A dermoscopic image of a skin lesion: 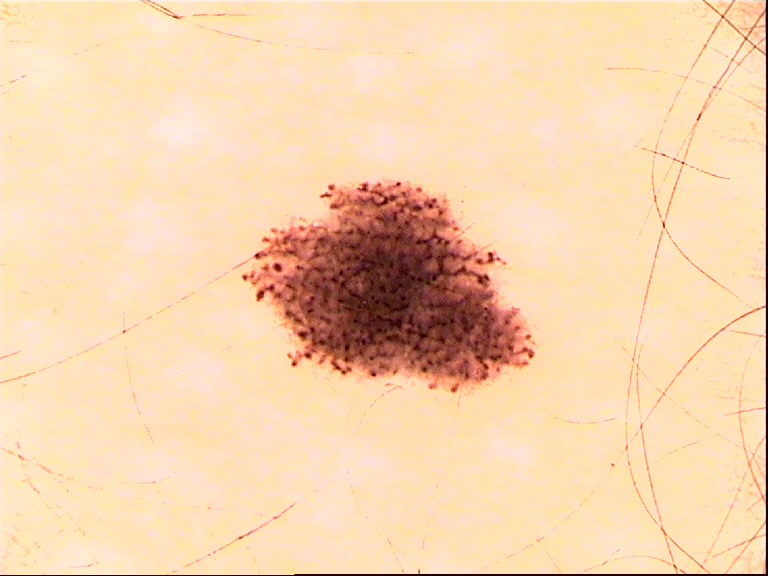Consistent with a dysplastic junctional nevus.